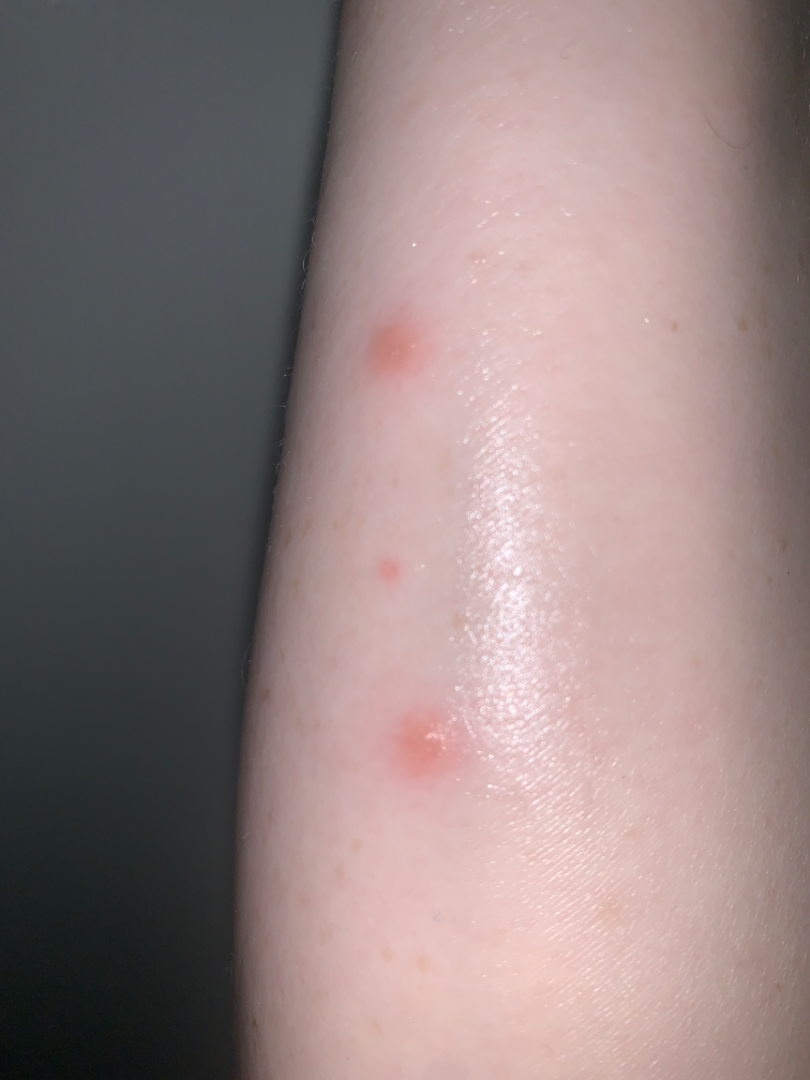<dermatology_case>
<differential>
  <Insect Bite>0.54</Insect Bite>
  <Herpes Zoster>0.23</Herpes Zoster>
  <Allergic Contact Dermatitis>0.23</Allergic Contact Dermatitis>
</differential>
</dermatology_case>